A female patient roughly 50 years of age; a dermoscopy image of a single skin lesion:
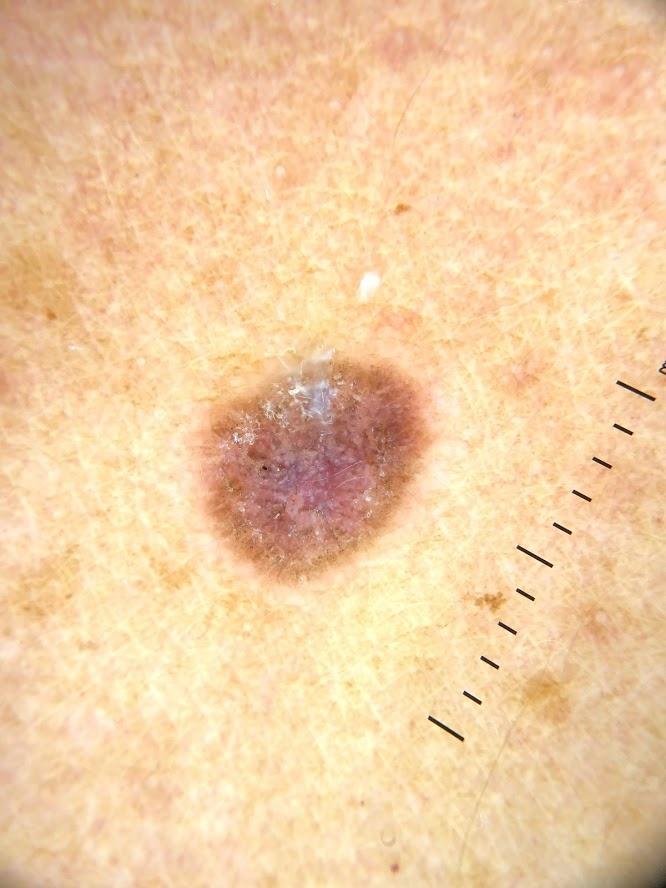Findings:
- body site · an upper extremity
- diagnostic label · Nevus (biopsy-proven)